The photograph is a close-up of the affected area — 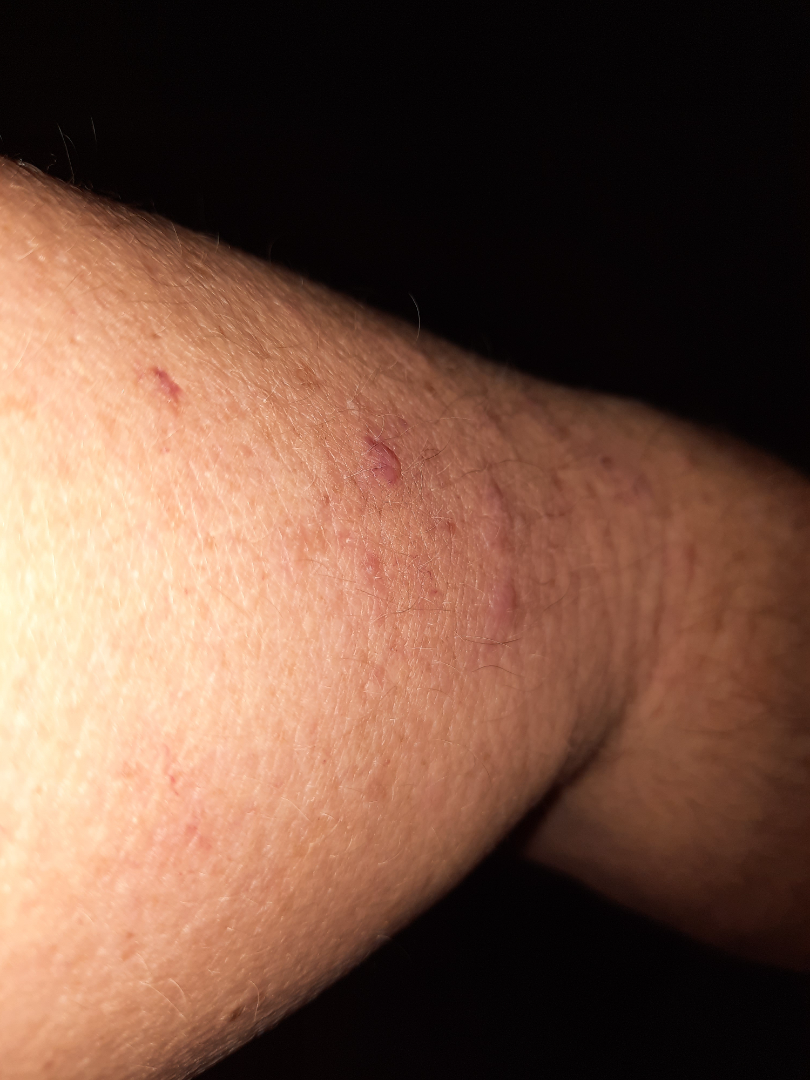{
  "assessment": "indeterminate from the photograph",
  "skin_tone": {
    "monk_skin_tone": [
      3,
      4
    ]
  }
}